The affected area is the back of the hand · this image was taken at a distance · the contributor is a female aged 18–29:
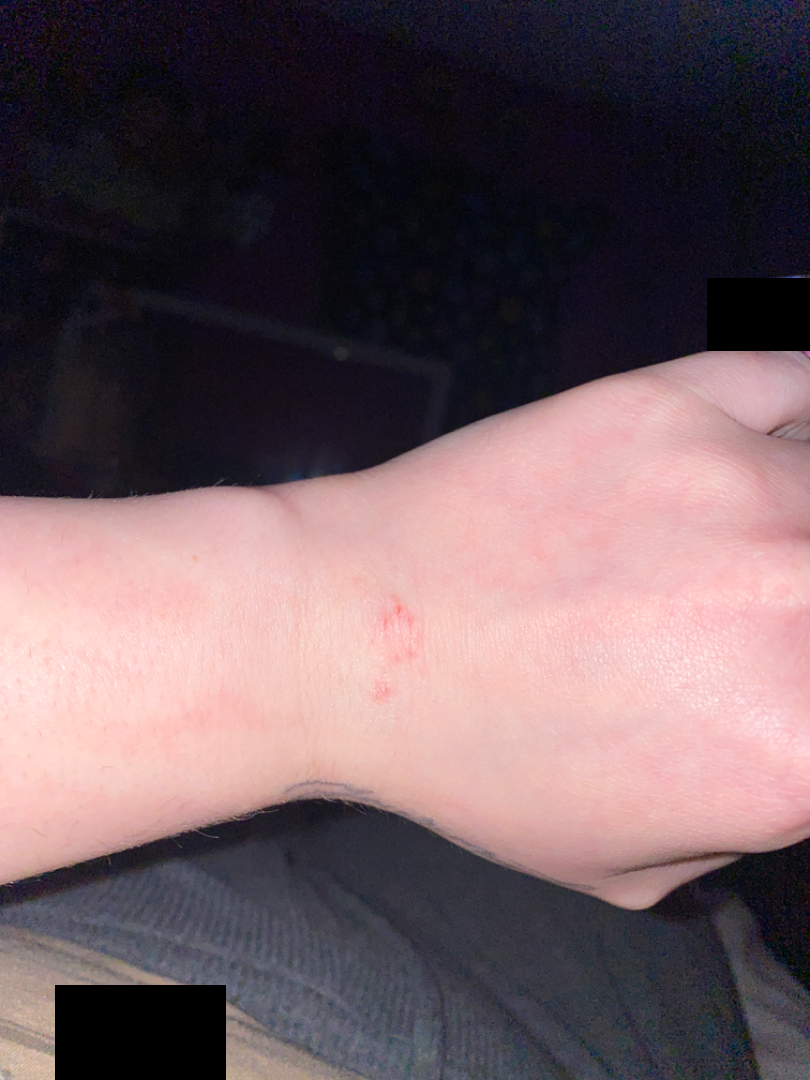On photographic review by a dermatologist: the favored diagnosis is Allergic Contact Dermatitis; possibly Irritant Contact Dermatitis.